A dermoscopy image of a single skin lesion.
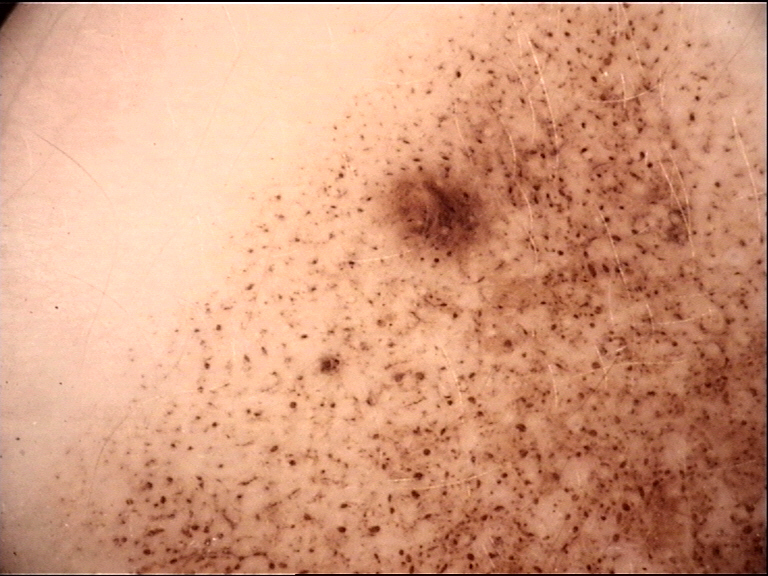Findings:
- assessment — congenital junctional nevus (expert consensus)